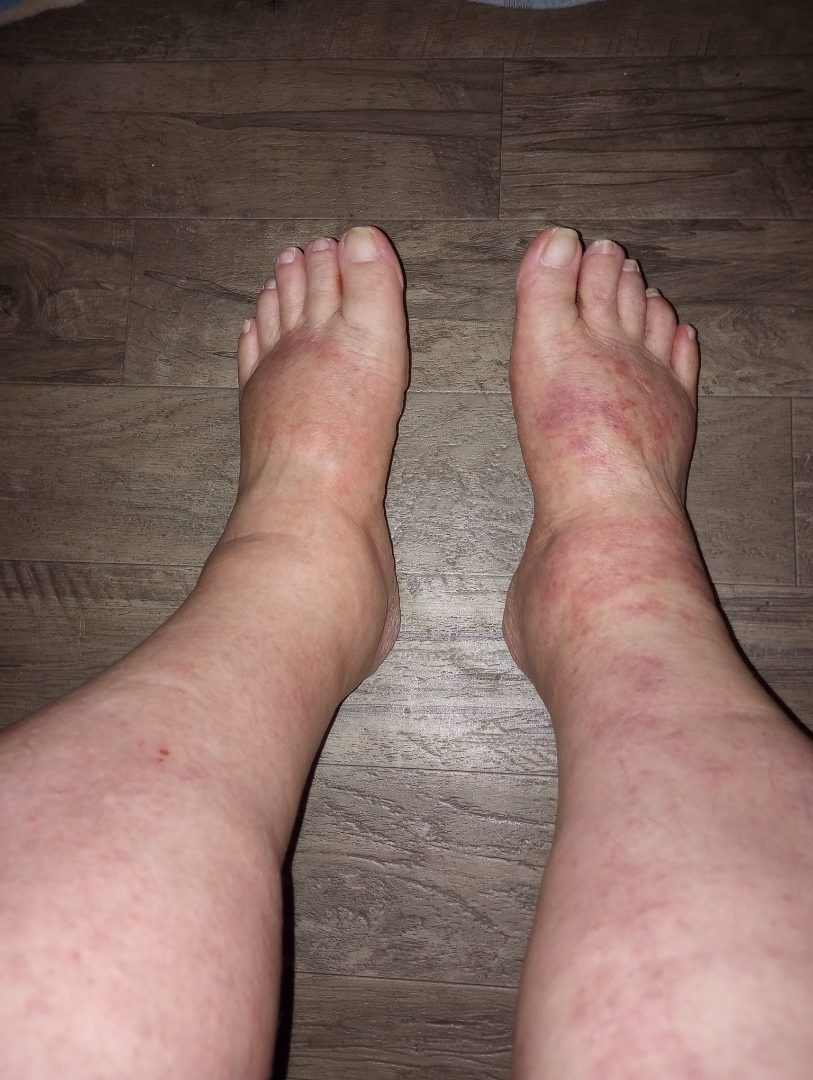The condition could not be reliably identified from the image.